A dermoscopic close-up of a skin lesion: 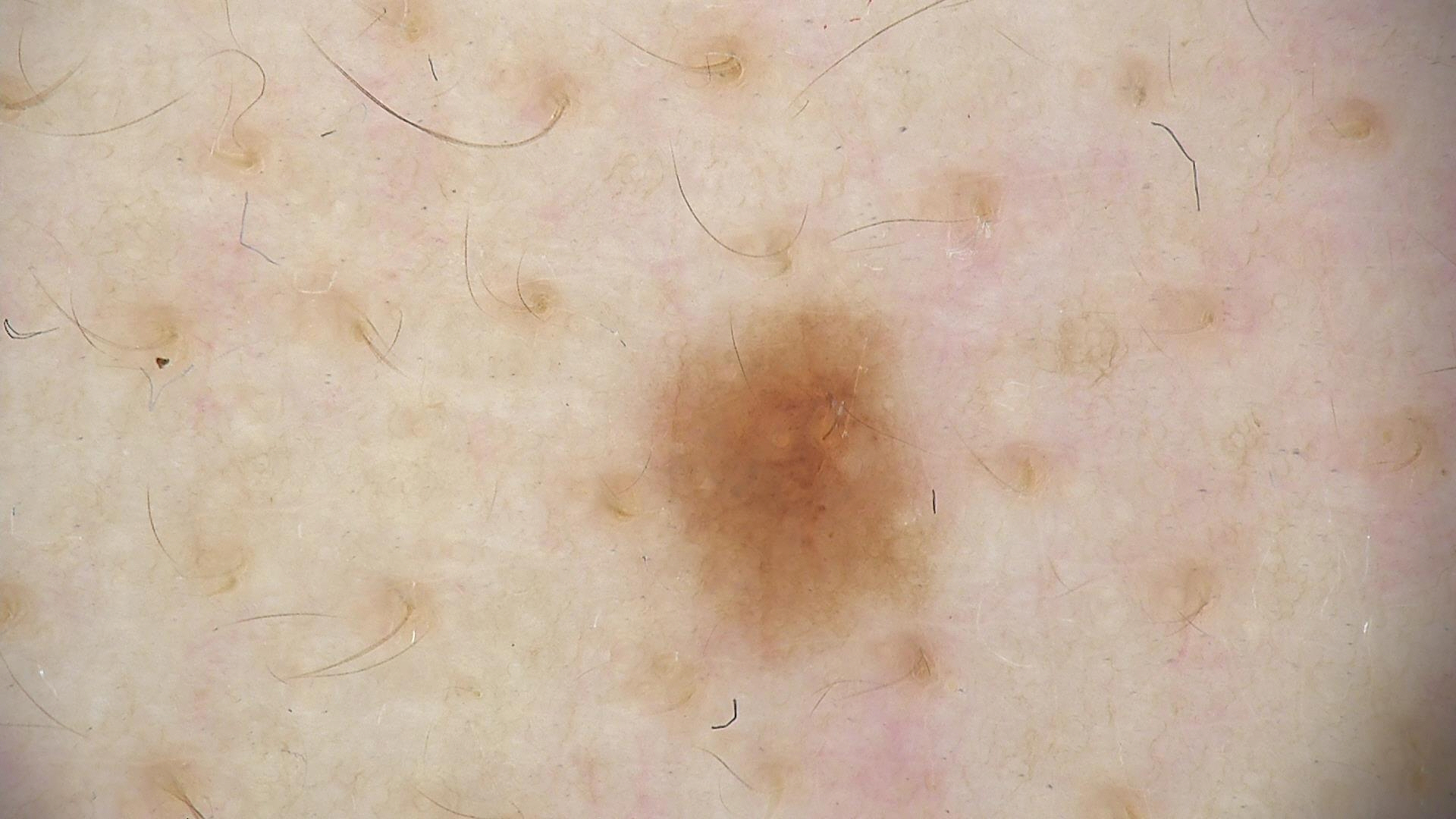Impression: Diagnosed as a dysplastic junctional nevus.